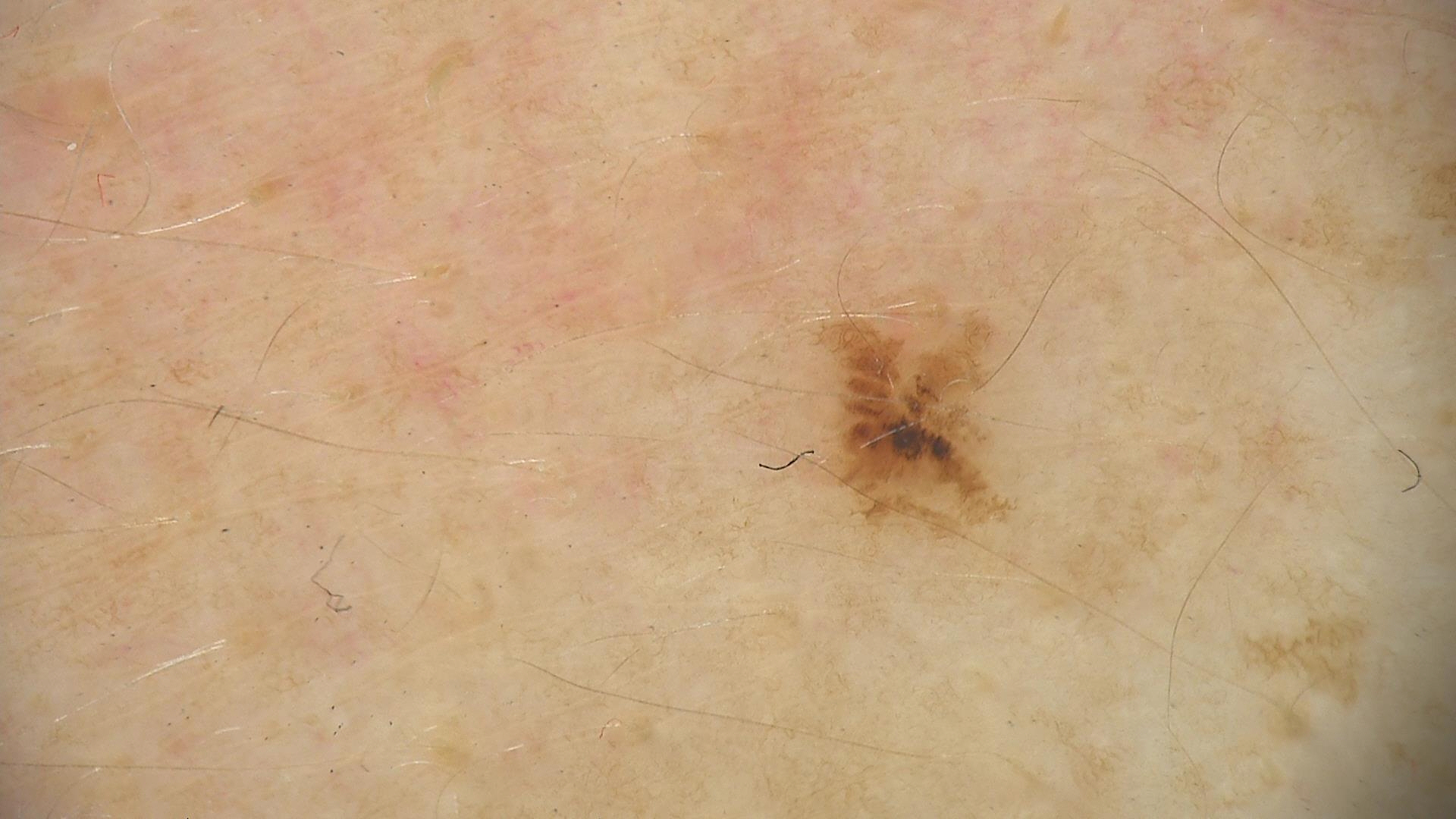class — dysplastic junctional nevus (expert consensus).